The photo was captured at a distance · skin tone: self-reported Fitzpatrick IV · male contributor, age 50–59:
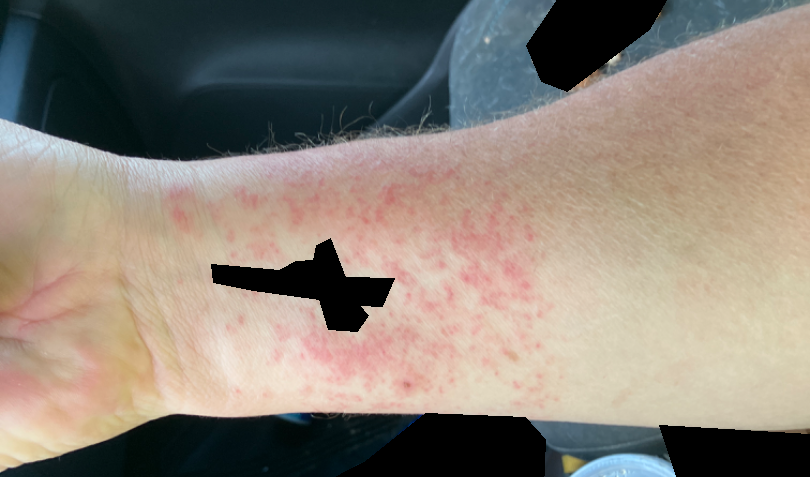assessment: not assessable.